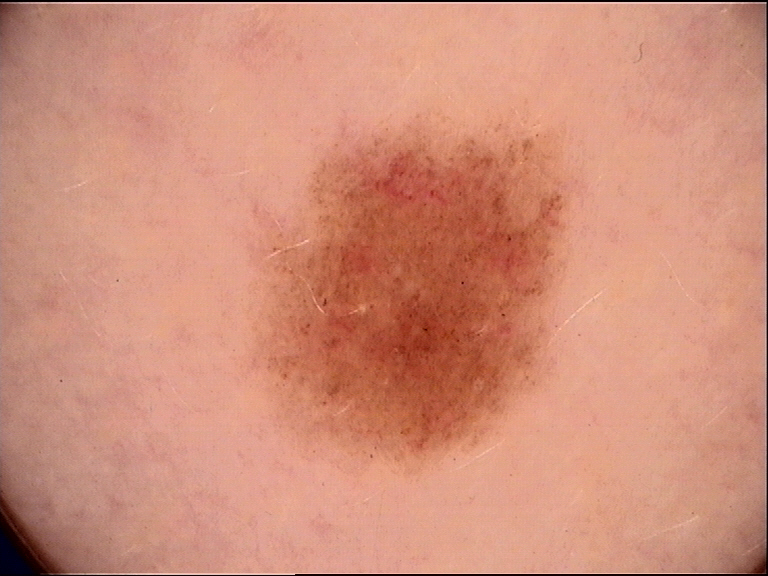The diagnosis was a dysplastic junctional nevus.